Dermoscopy of a skin lesion.
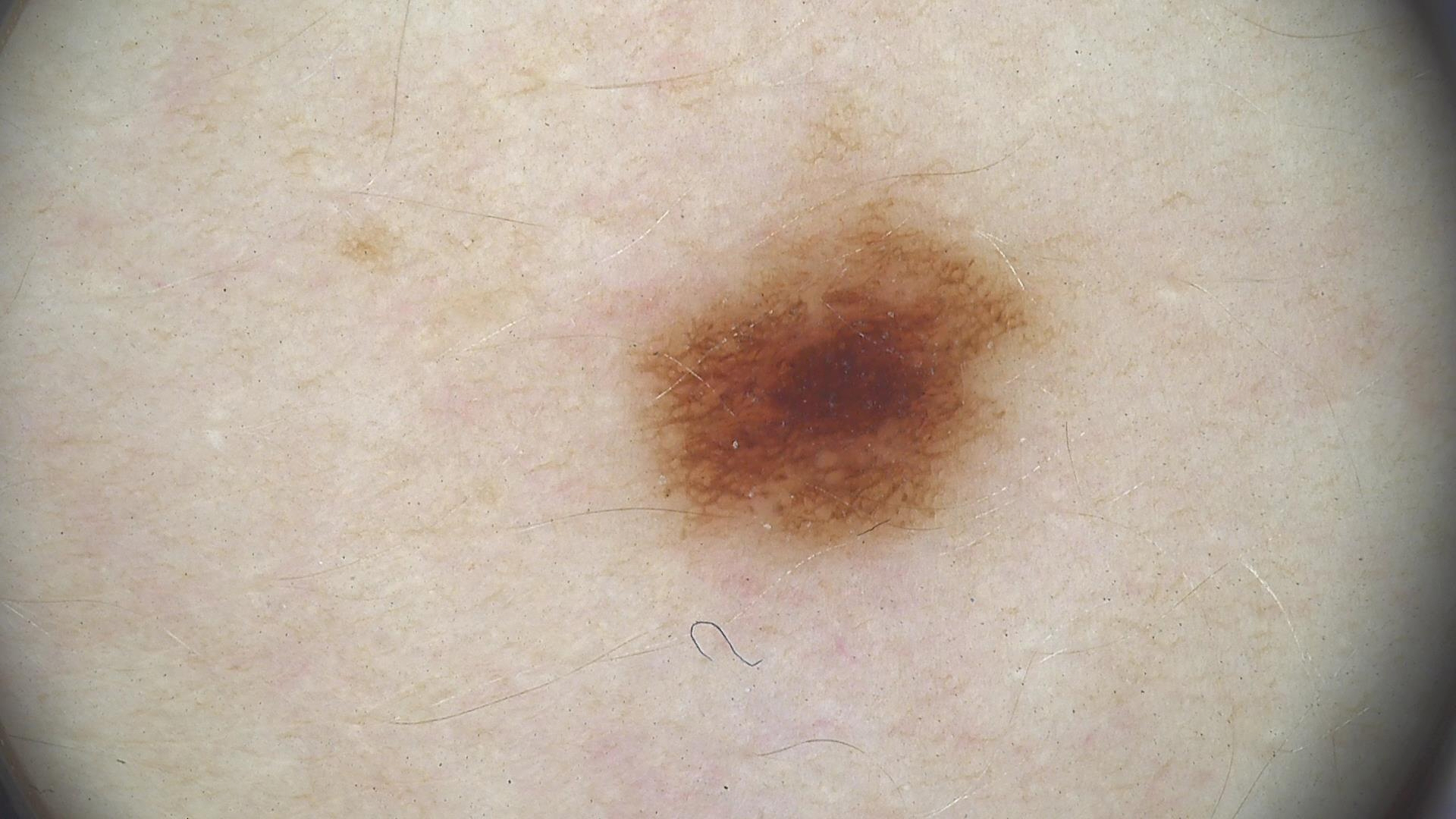Classified as a benign lesion — a dysplastic junctional nevus.